This image was taken at an angle: 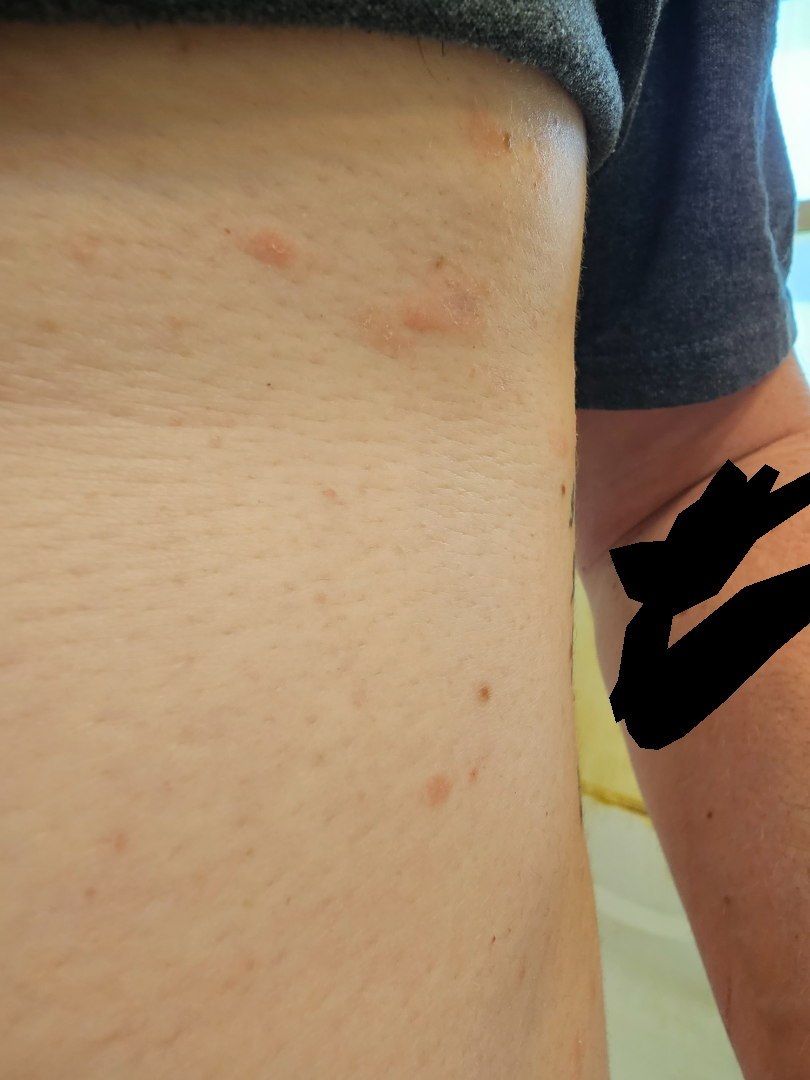<dermatology_case>
  <skin_tone>
    <fitzpatrick>II</fitzpatrick>
    <monk_skin_tone>2</monk_skin_tone>
  </skin_tone>
  <differential>
    <tied_lead>Eczema, Psoriasis, Pityriasis lichenoides</tied_lead>
  </differential>
</dermatology_case>